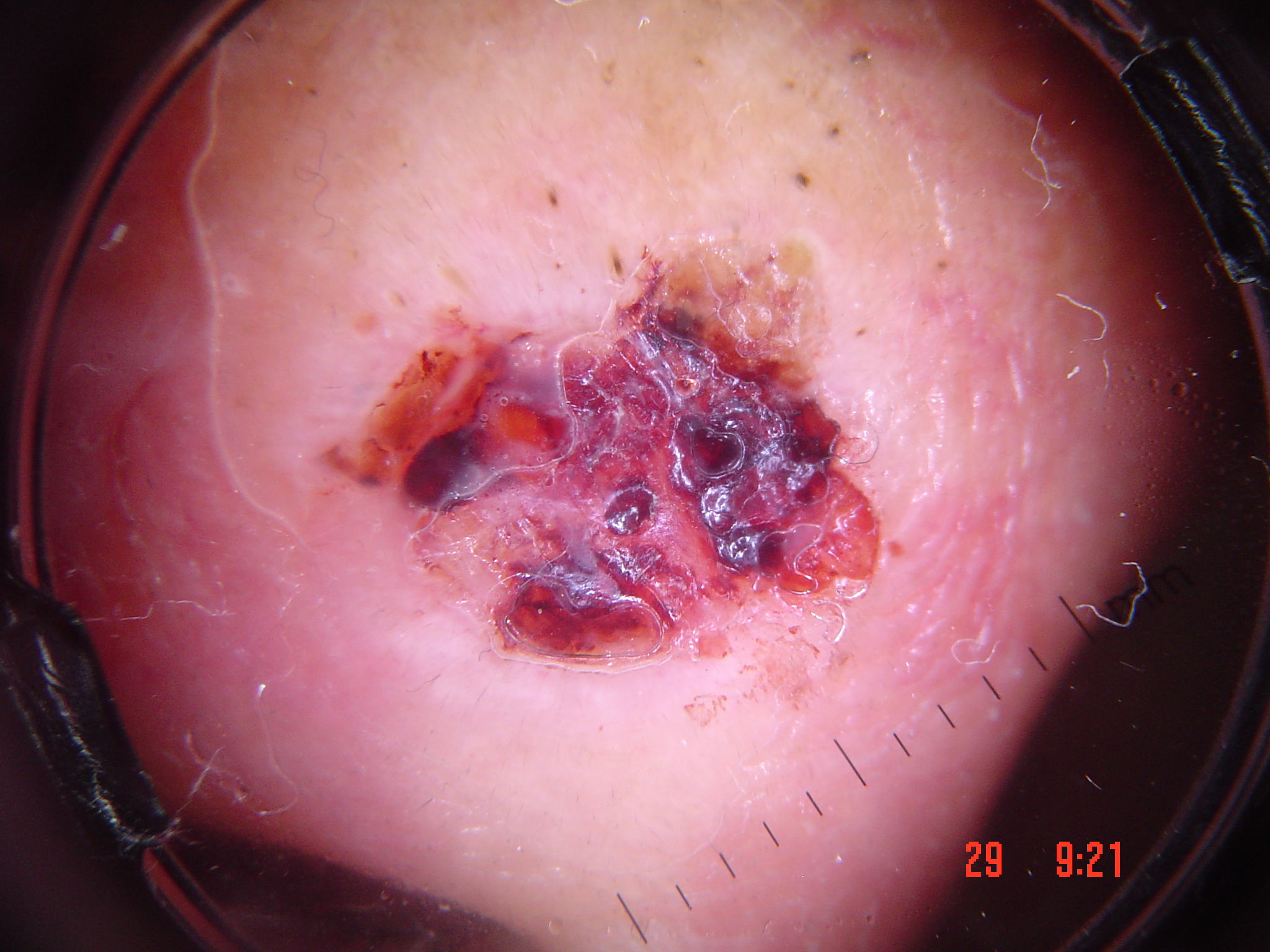Pathology: Biopsy-confirmed as a squamous cell carcinoma.